Close-up view — 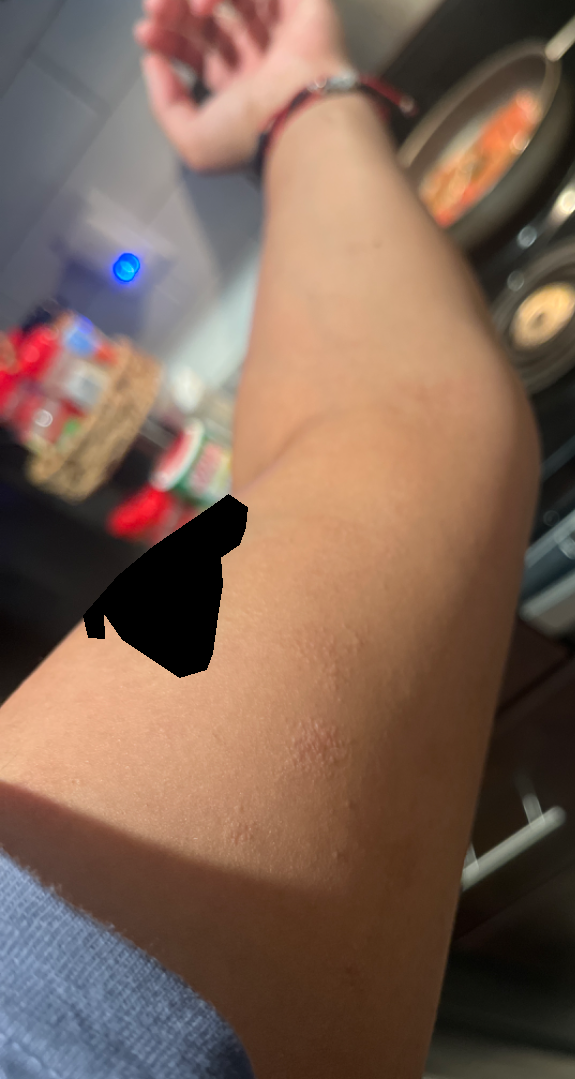The image was not sufficient for the reviewer to characterize the skin condition.